A dermoscopy image of a single skin lesion.
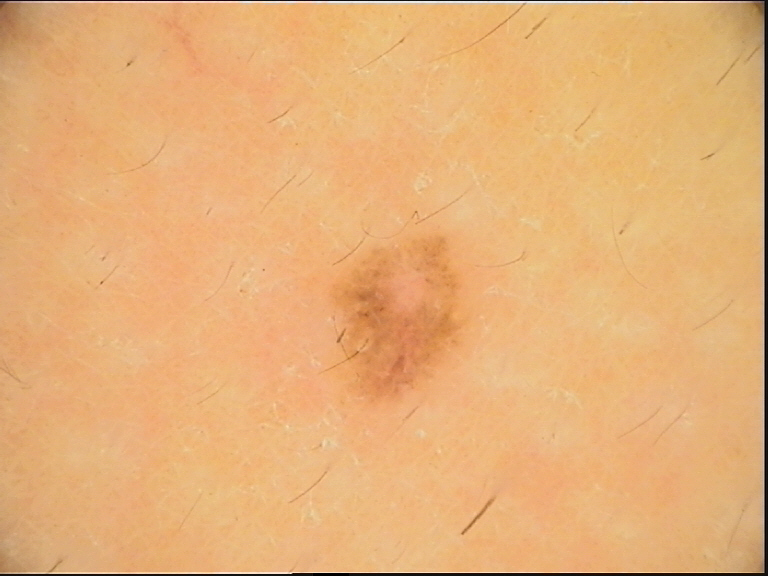Classified as a benign lesion — a dysplastic junctional nevus.